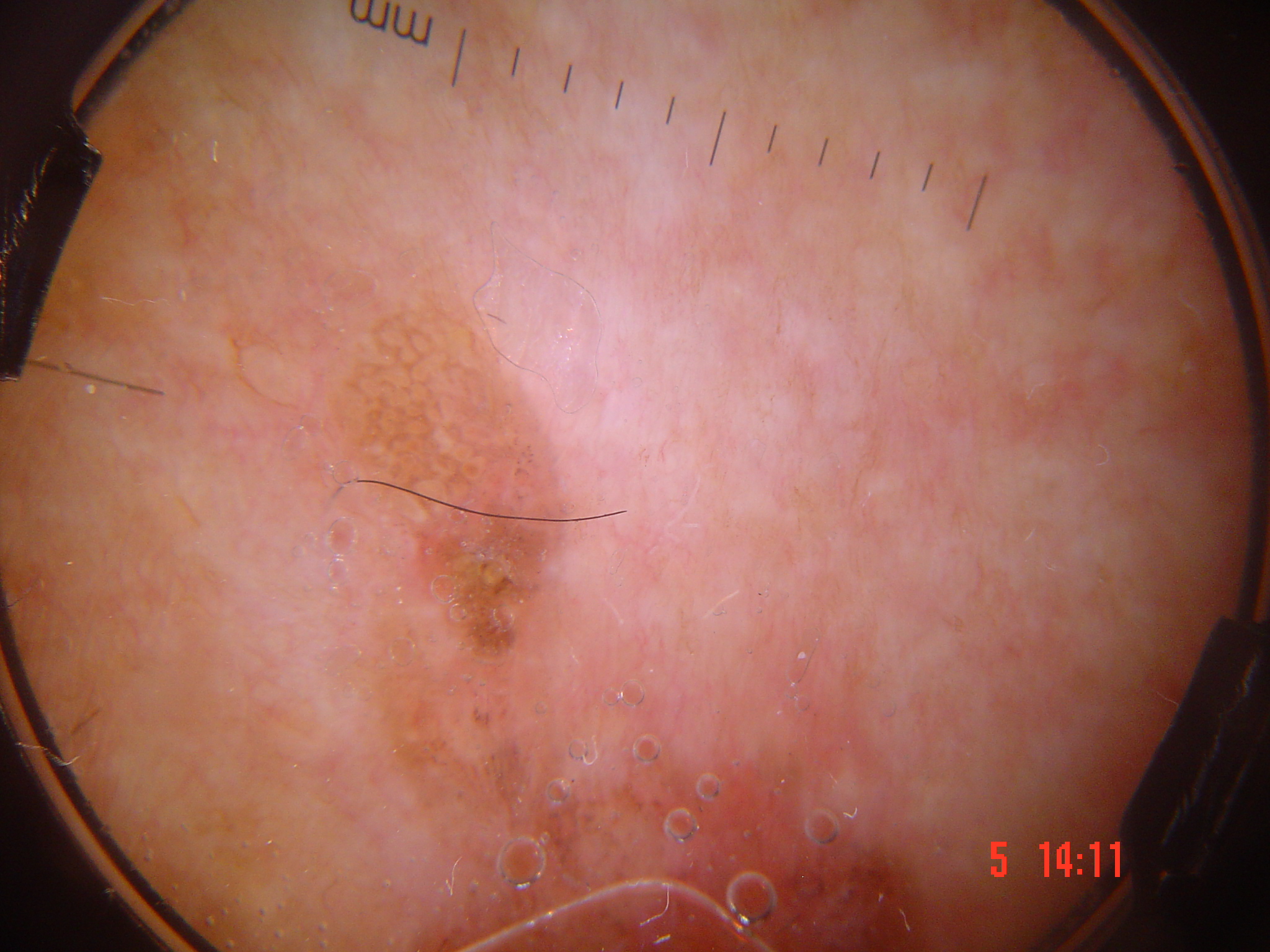Dermoscopy of a skin lesion.
This is a keratinocytic lesion.
Confirmed on histopathology as Bowen's disease.